A dermoscopic photograph of a skin lesion.
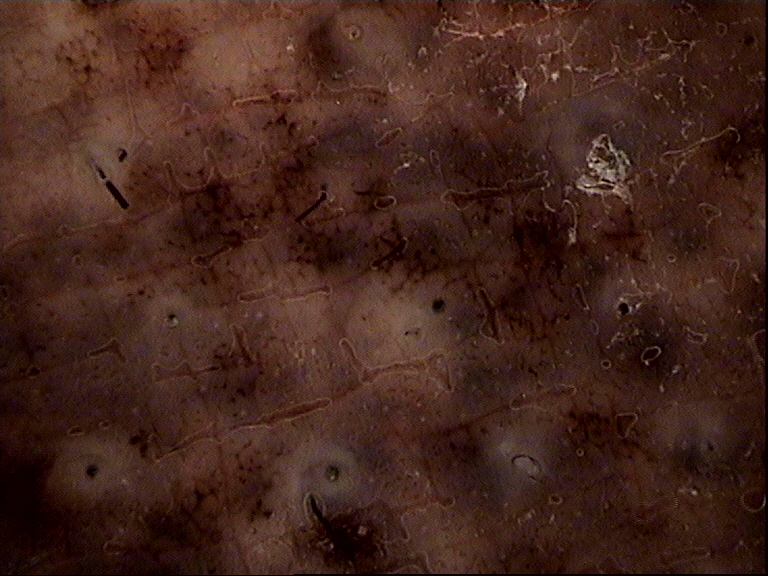label=congenital compound nevus (expert consensus).